A male patient about 75 years old.
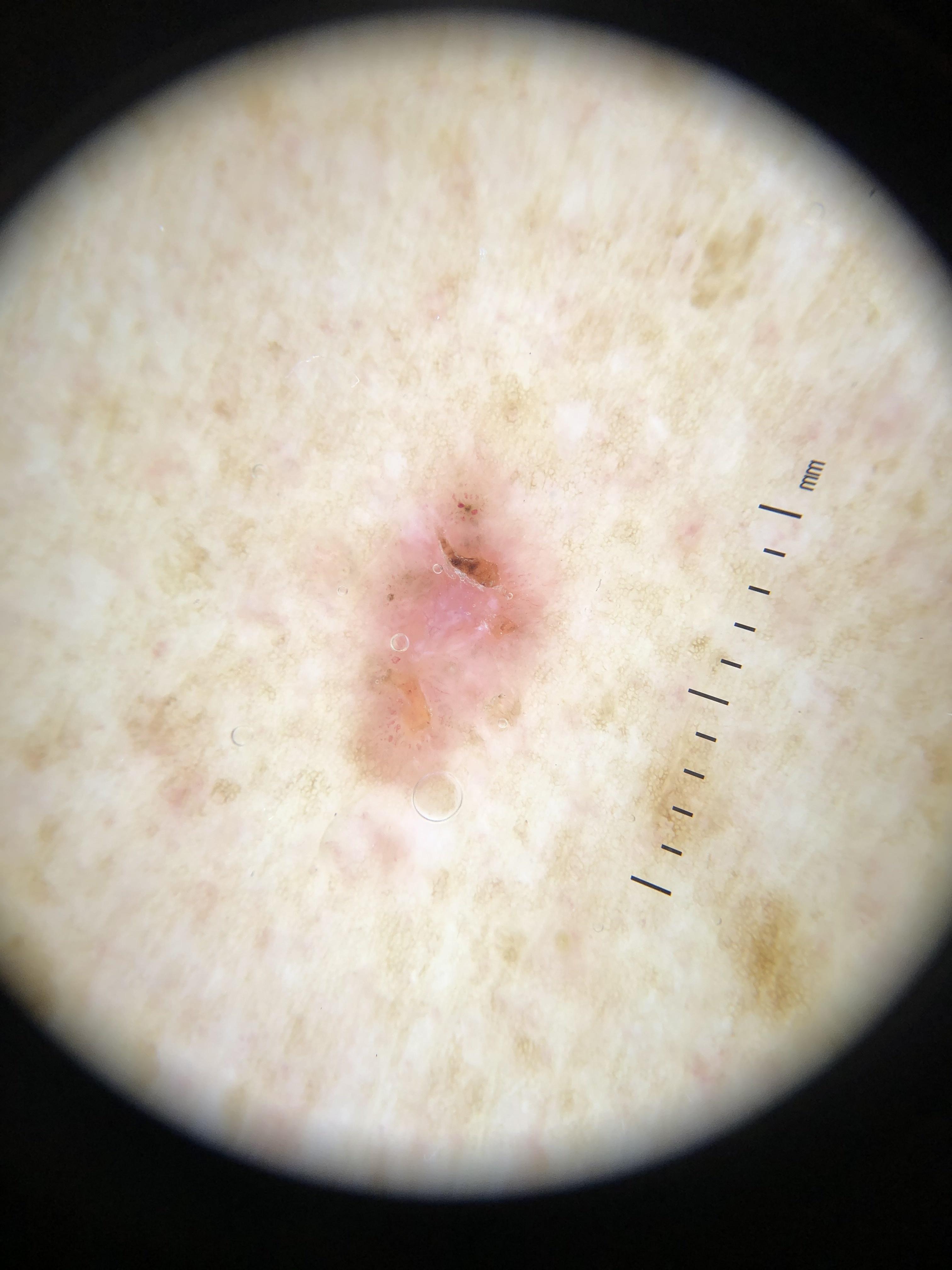  lesion_location:
    region: the trunk
  diagnosis:
    name: Basal cell carcinoma
    malignancy: malignant
    confirmation: histopathology
    lineage: adnexal